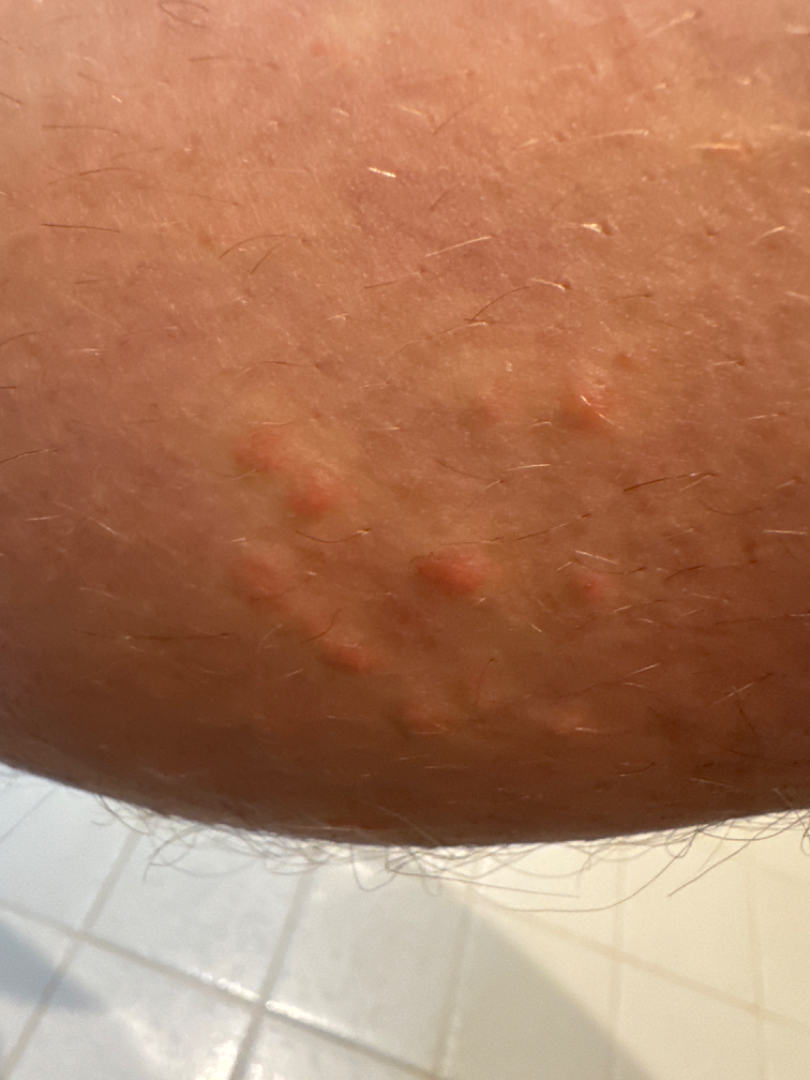Patient information:
FST II; lay reviewers estimated 2 on the Monk skin tone scale. The patient notes itching. The patient described the issue as a rash. The leg is involved. No associated systemic symptoms reported. The patient notes the lesion is raised or bumpy. The contributor is 30–39, male. The condition has been present for less than one week. The photograph was taken at an angle.
Review:
Insect Bite (67%); Hypersensitivity (33%).